A dermoscopy image of a single skin lesion.
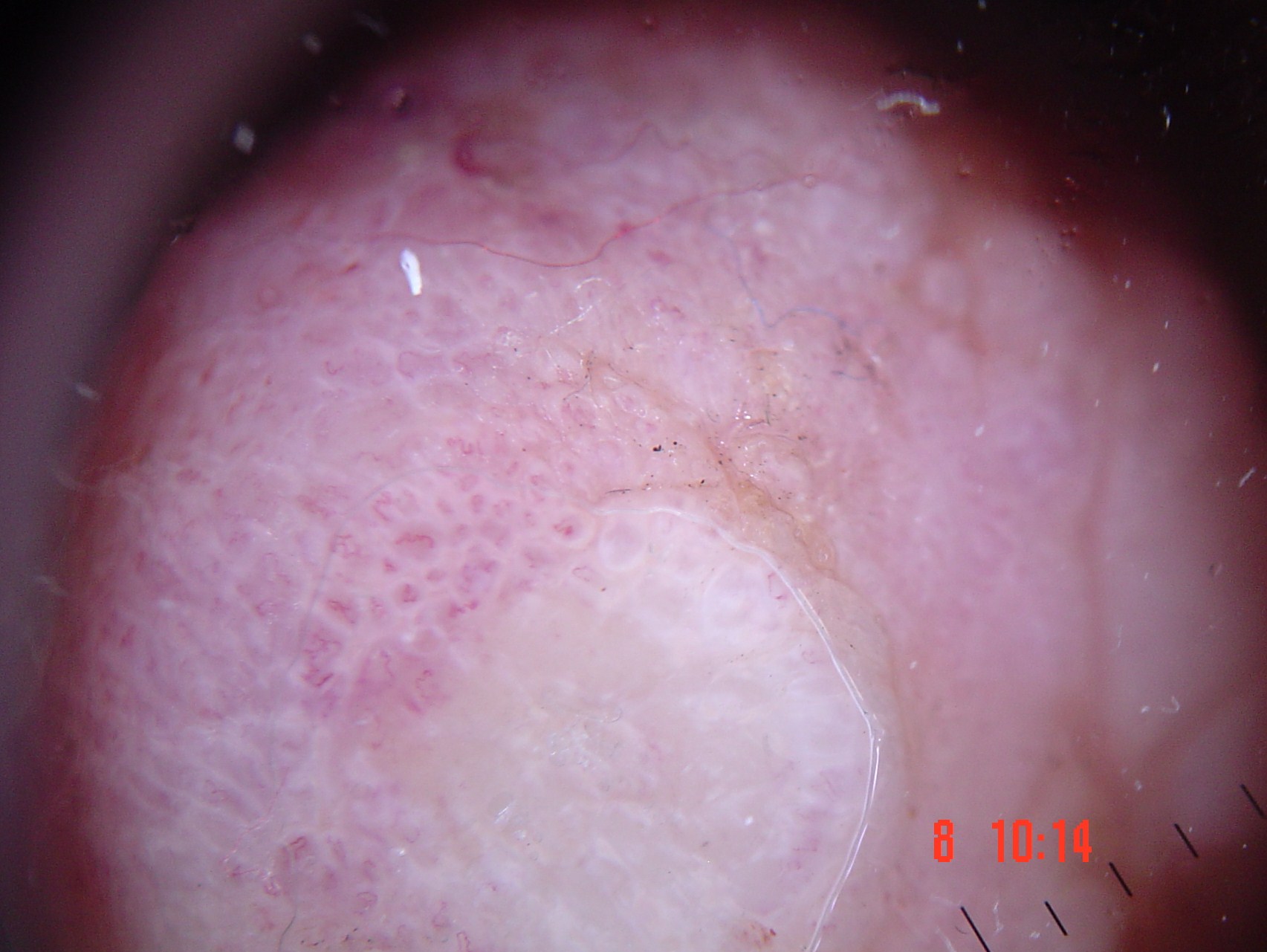Confirmed on histopathology as an acral nodular melanoma.